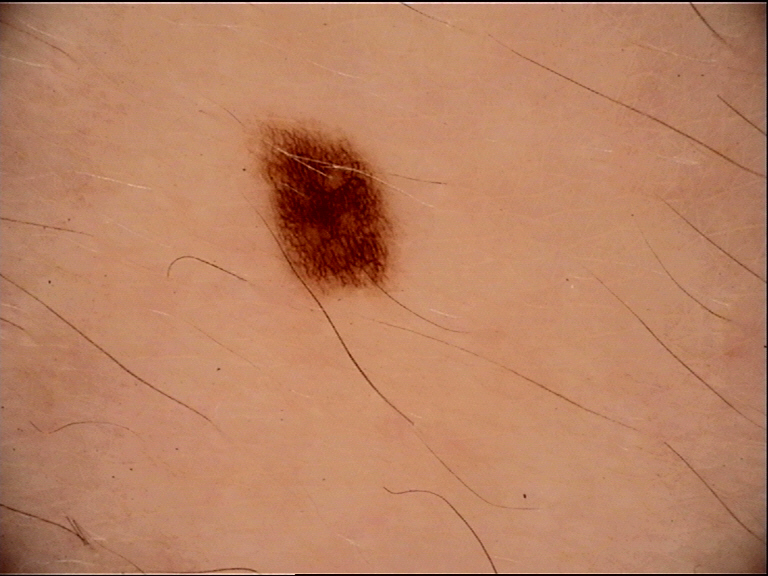Summary: A dermoscopic image of a skin lesion. Impression: Diagnosed as a benign lesion — a dysplastic junctional nevus.